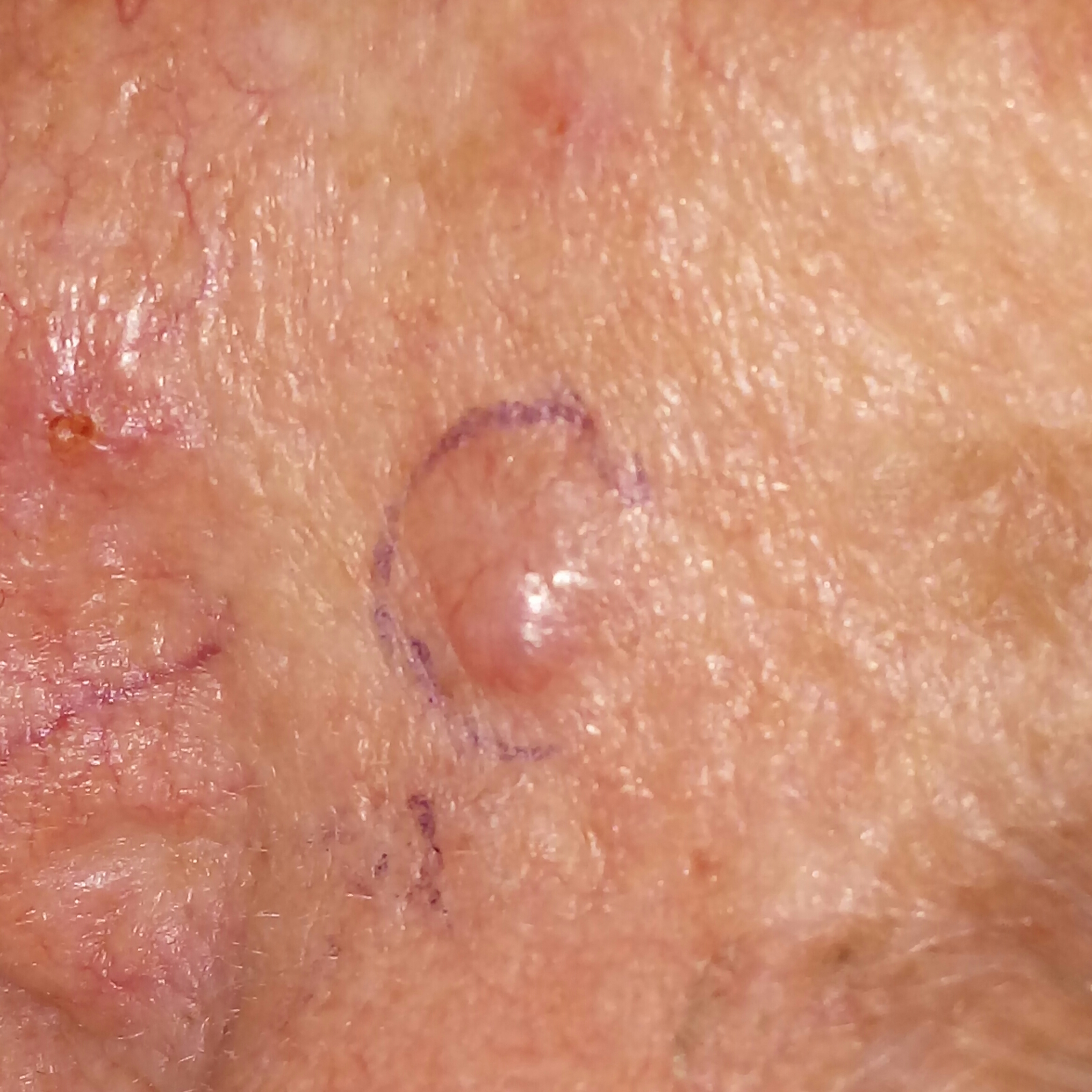subject: male, aged 71 | imaging: clinical photograph | skin type: II | site: the nose | size: 7x5 mm | reported symptoms: elevation | diagnosis: basal cell carcinoma (biopsy-proven).